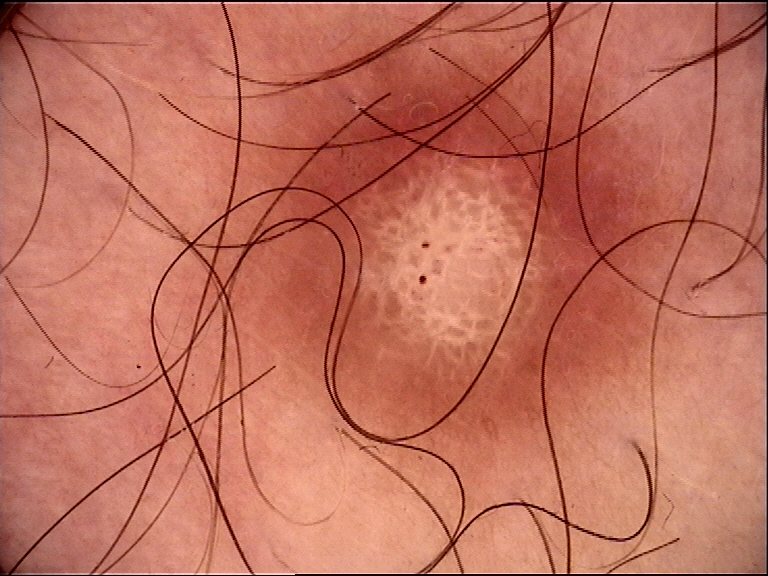Findings:
A dermoscopic image of a skin lesion. This is a fibro-histiocytic lesion.
Conclusion:
Classified as a dermatofibroma.